The patient is a male aged around 70; this is a dermoscopic photograph of a skin lesion:
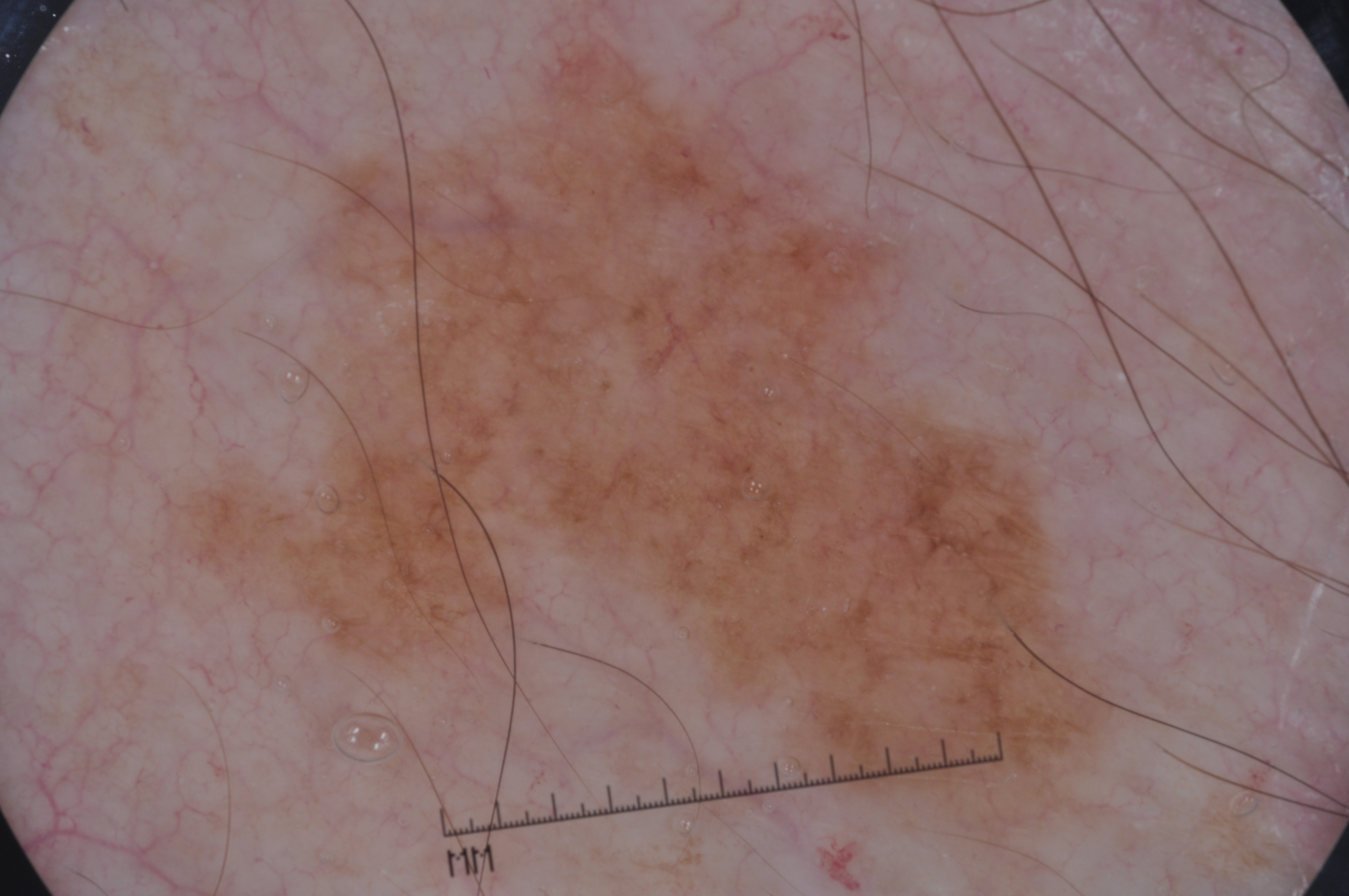Findings: As (left, top, right, bottom), the lesion's extent is [179,35,1117,833]. Dermoscopically, the lesion shows milia-like cysts and pigment network. Conclusion: On biopsy, the diagnosis was a melanoma.